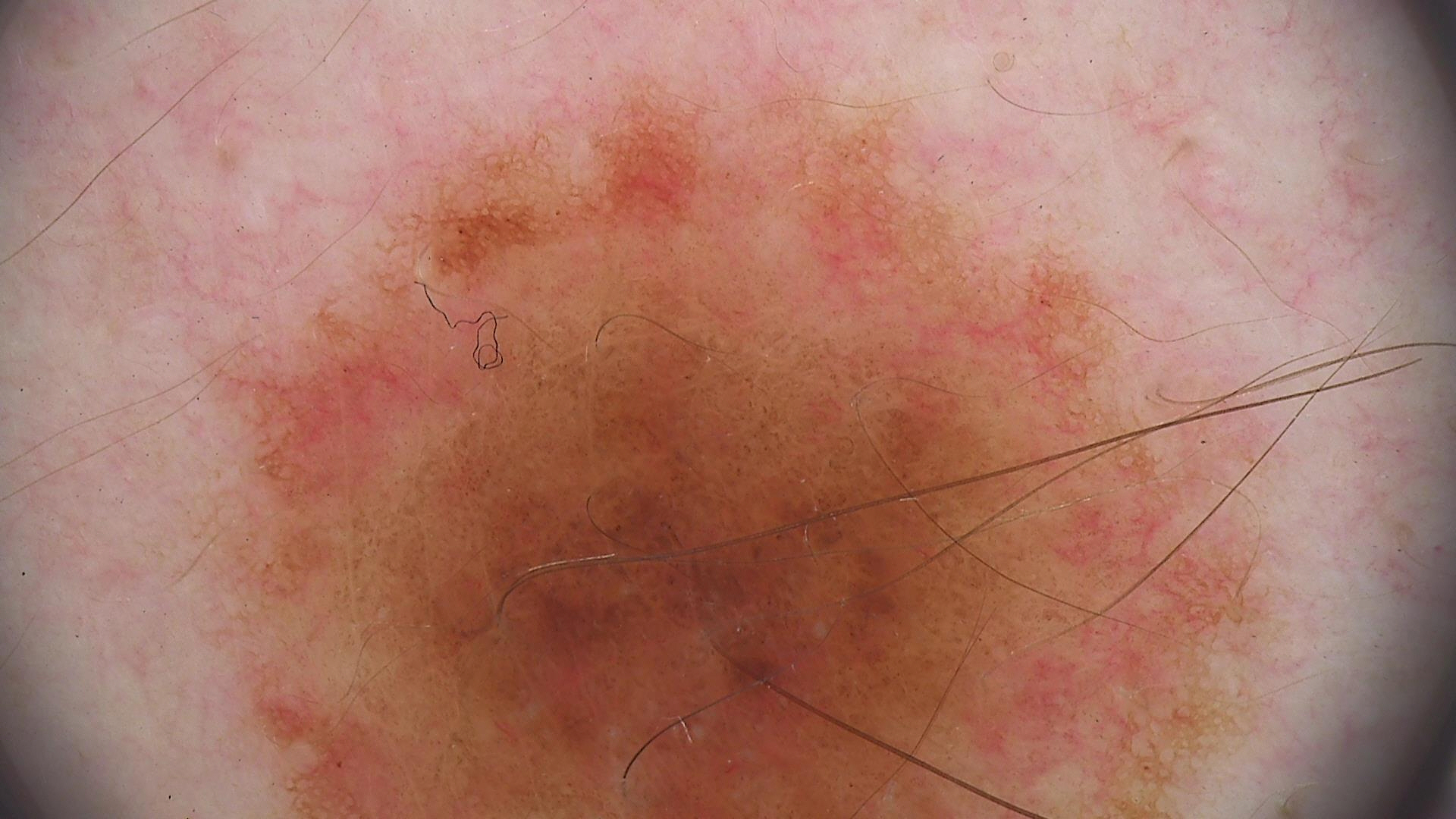Impression:
The diagnostic label was a dysplastic compound nevus.